Dermoscopy of a skin lesion:
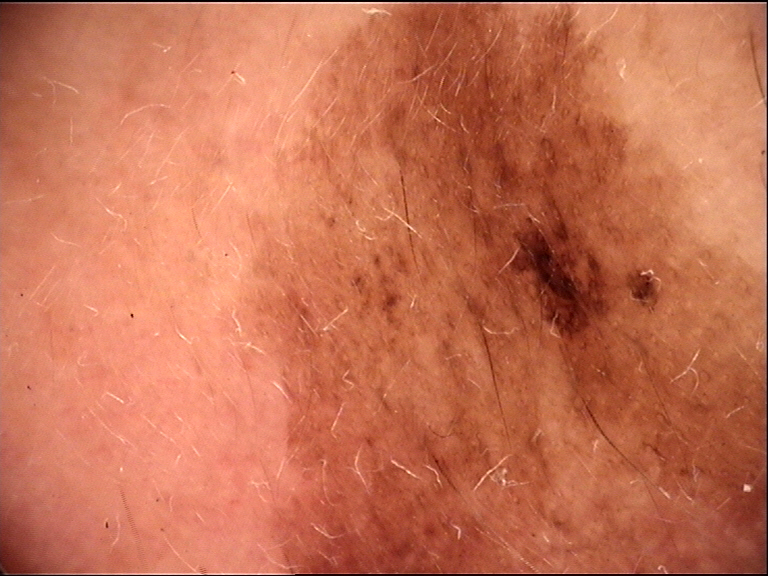The biopsy diagnosis was a malignancy — a lentigo maligna.